A clinical photograph showing a skin lesion · a male patient in their 70s.
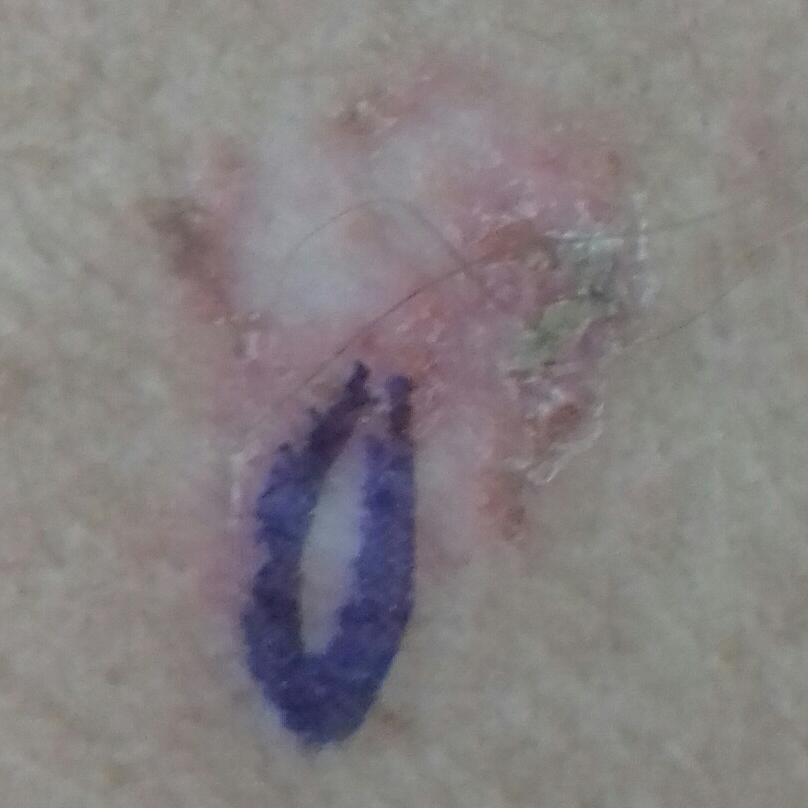The lesion is located on the back.
By the patient's account, the lesion is not elevated and has not bled.
On biopsy, the diagnosis was a squamous cell carcinoma.